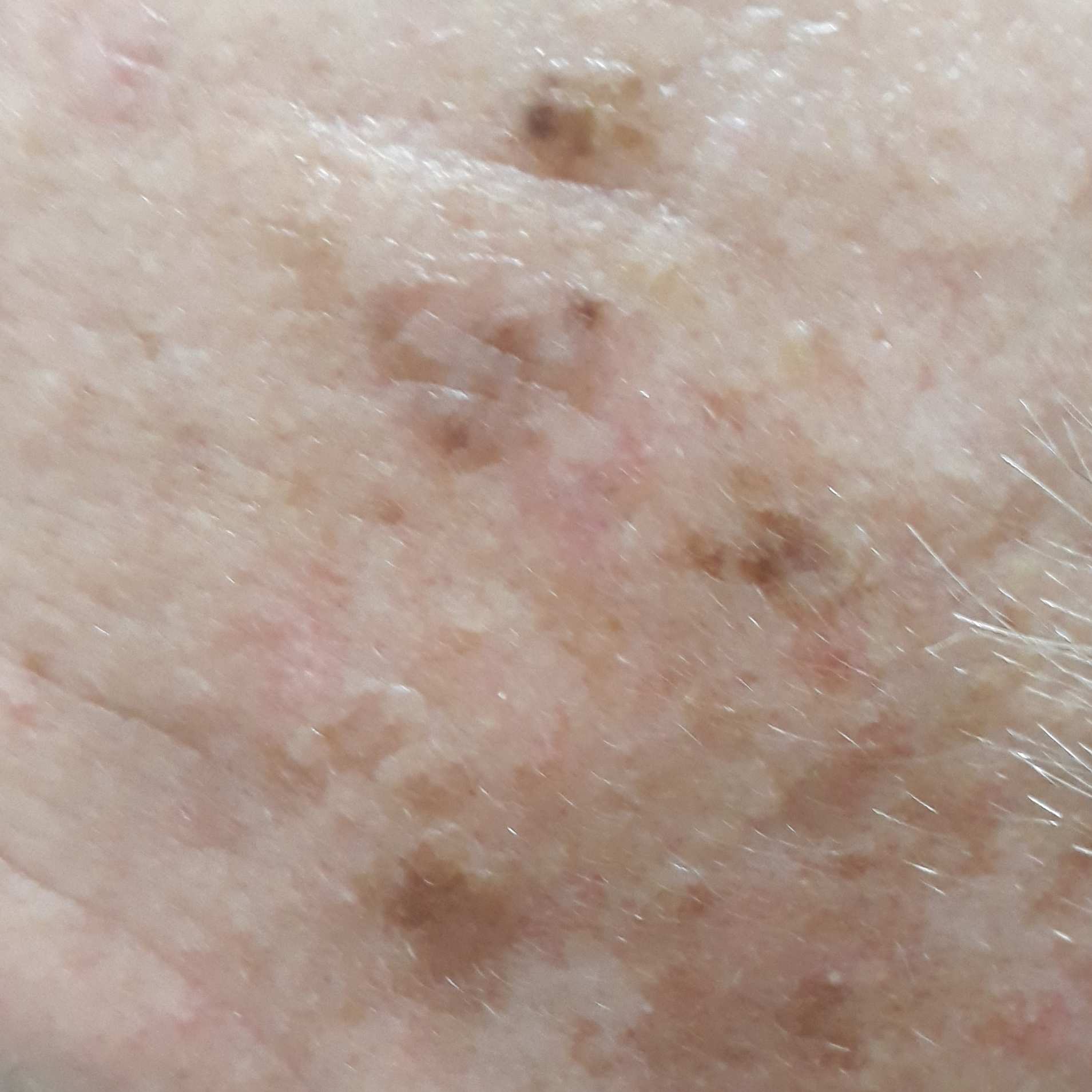A patient aged 60.
A clinical close-up photograph of a skin lesion.
The lesion involves the face.
No symptoms reported.
Consistent with a seborrheic keratosis.